A dermoscopic photograph of a skin lesion: 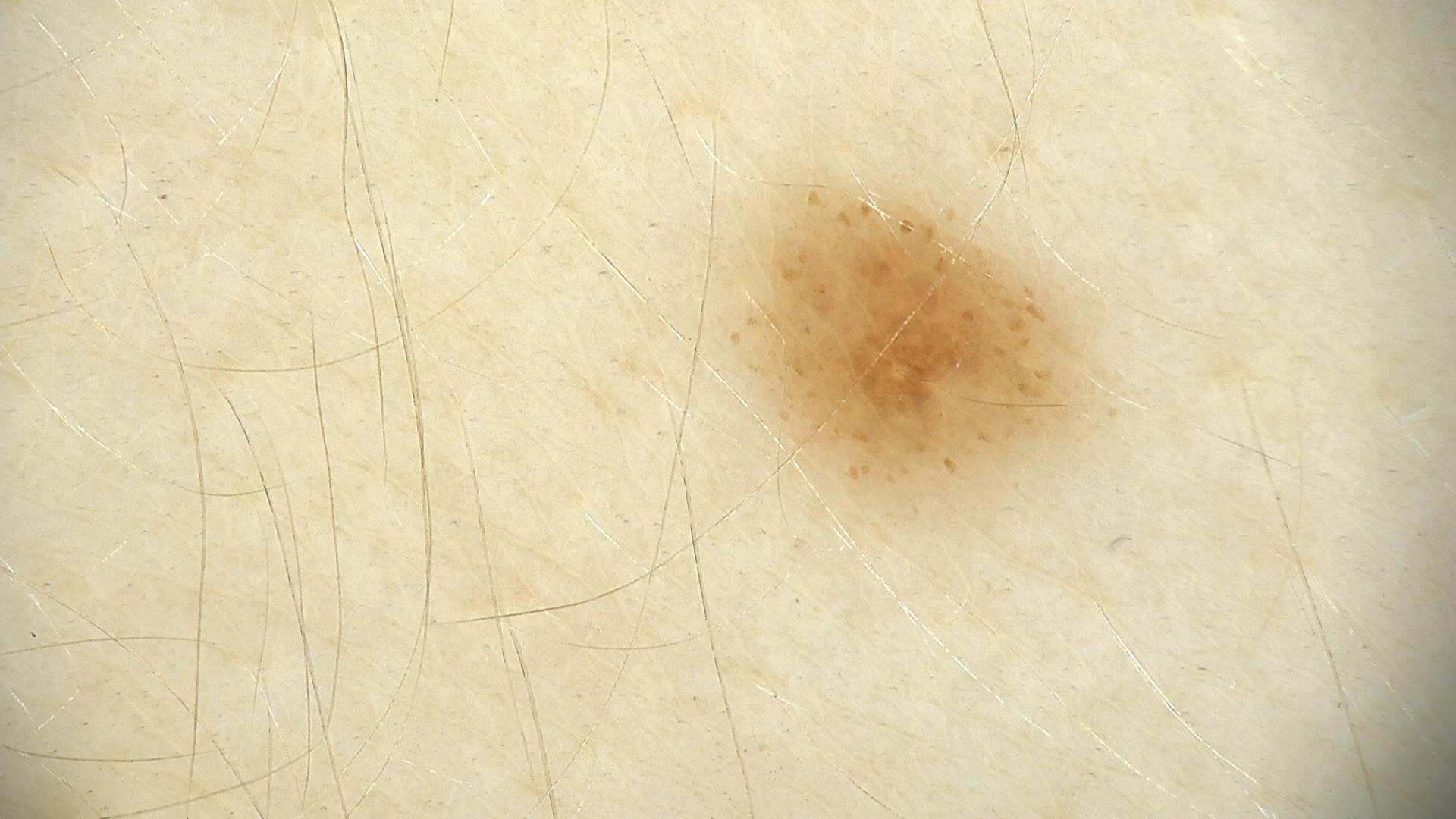assessment = dysplastic junctional nevus (expert consensus)